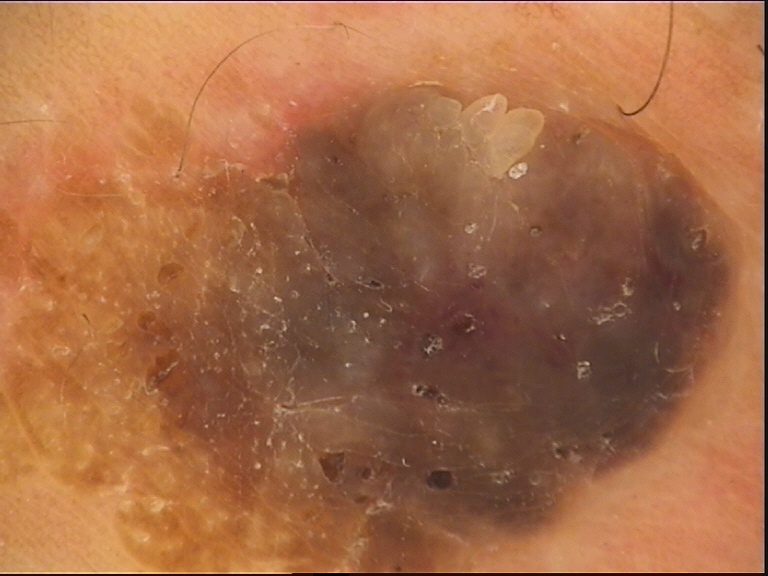This is a keratinocytic lesion.
The diagnosis was a benign lesion — a seborrheic keratosis.